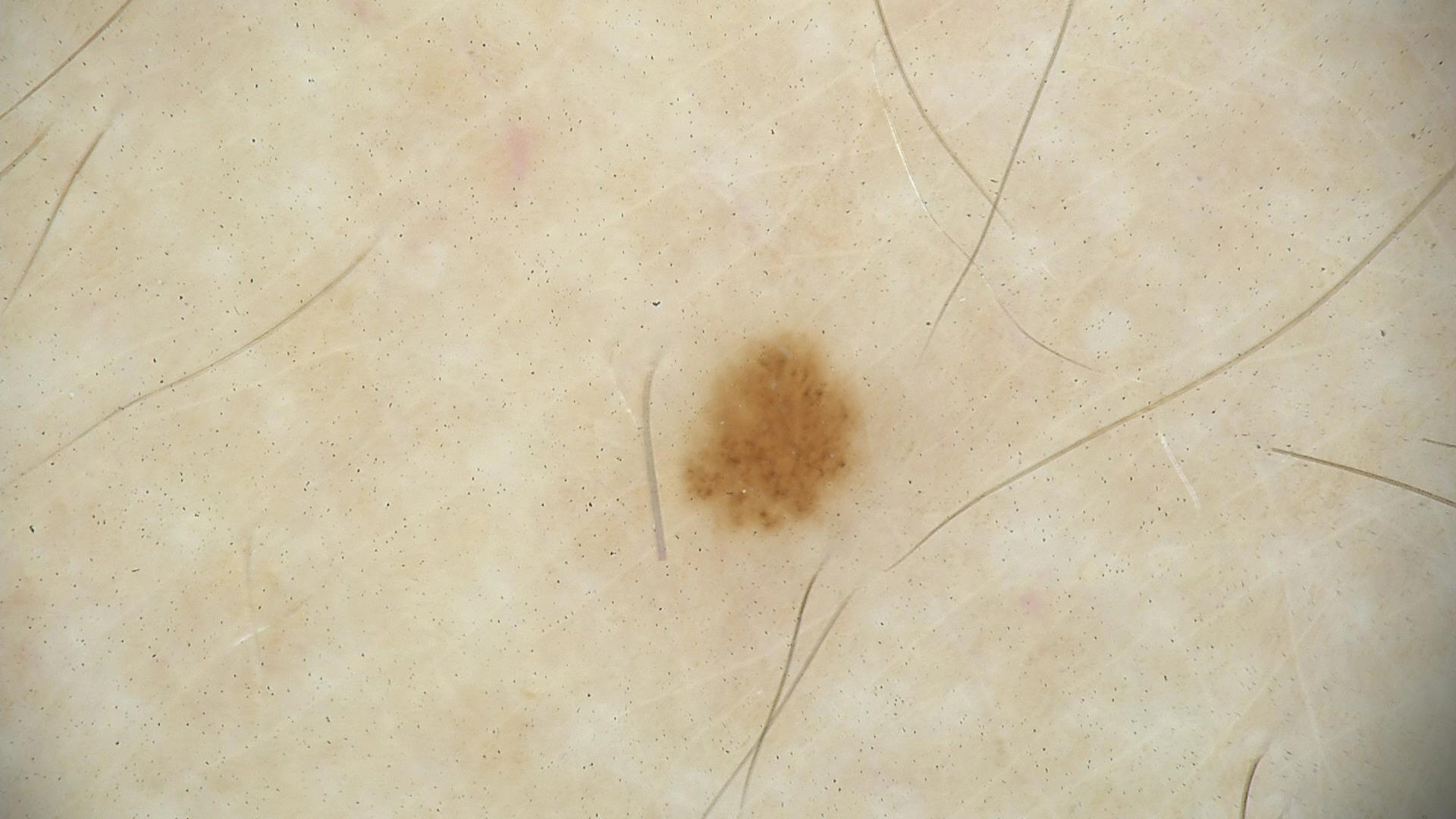Q: What kind of image is this?
A: dermoscopy
Q: What is this lesion?
A: dysplastic junctional nevus (expert consensus)